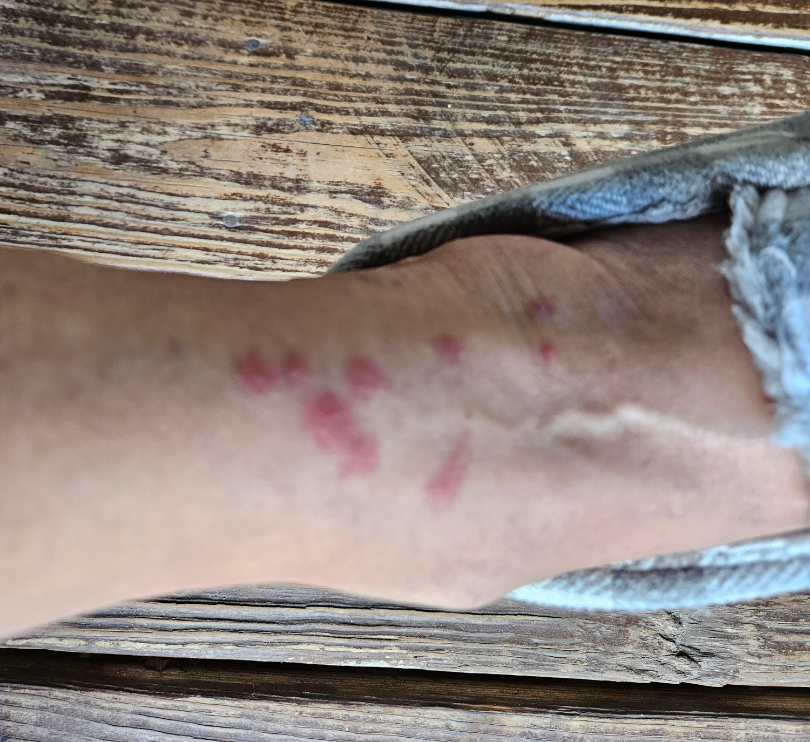| field | value |
|---|---|
| assessment | indeterminate |
| framing | close-up |